A dermoscopic image of a skin lesion: 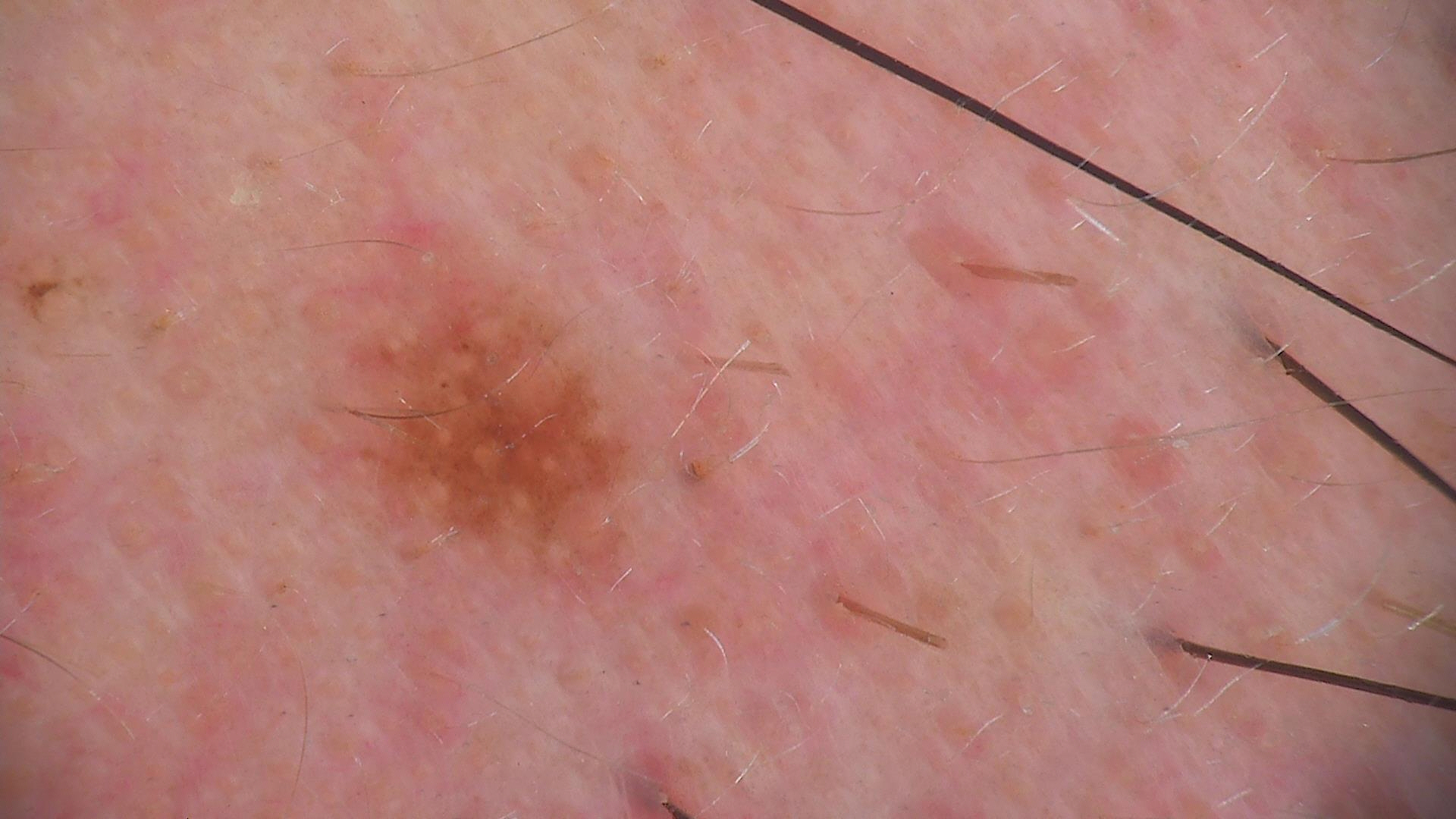Q: What is the lesion category?
A: banal, compound
Q: What is this lesion?
A: Miescher nevus (expert consensus)